A female patient aged around 70.
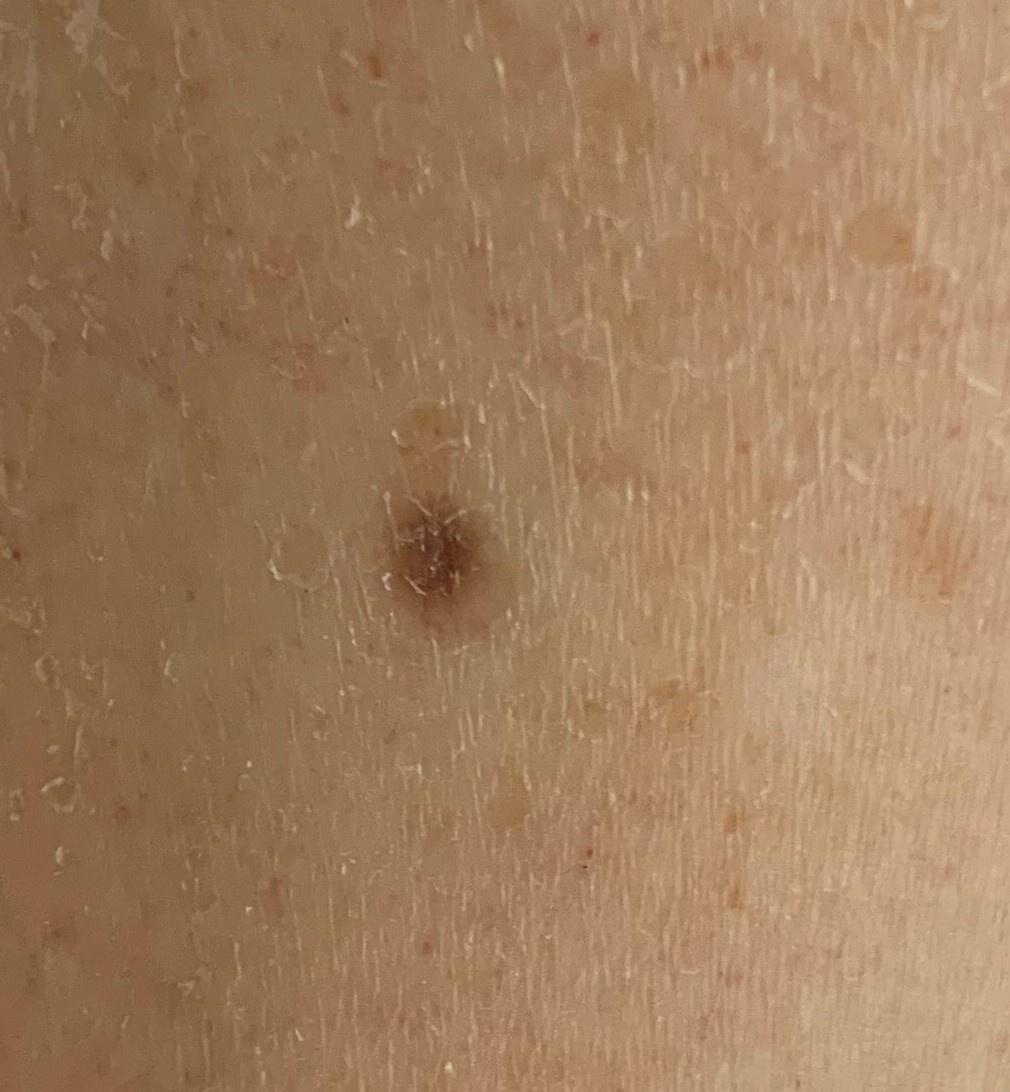Case:
– anatomic site — a lower extremity
– impression — Dermatofibroma